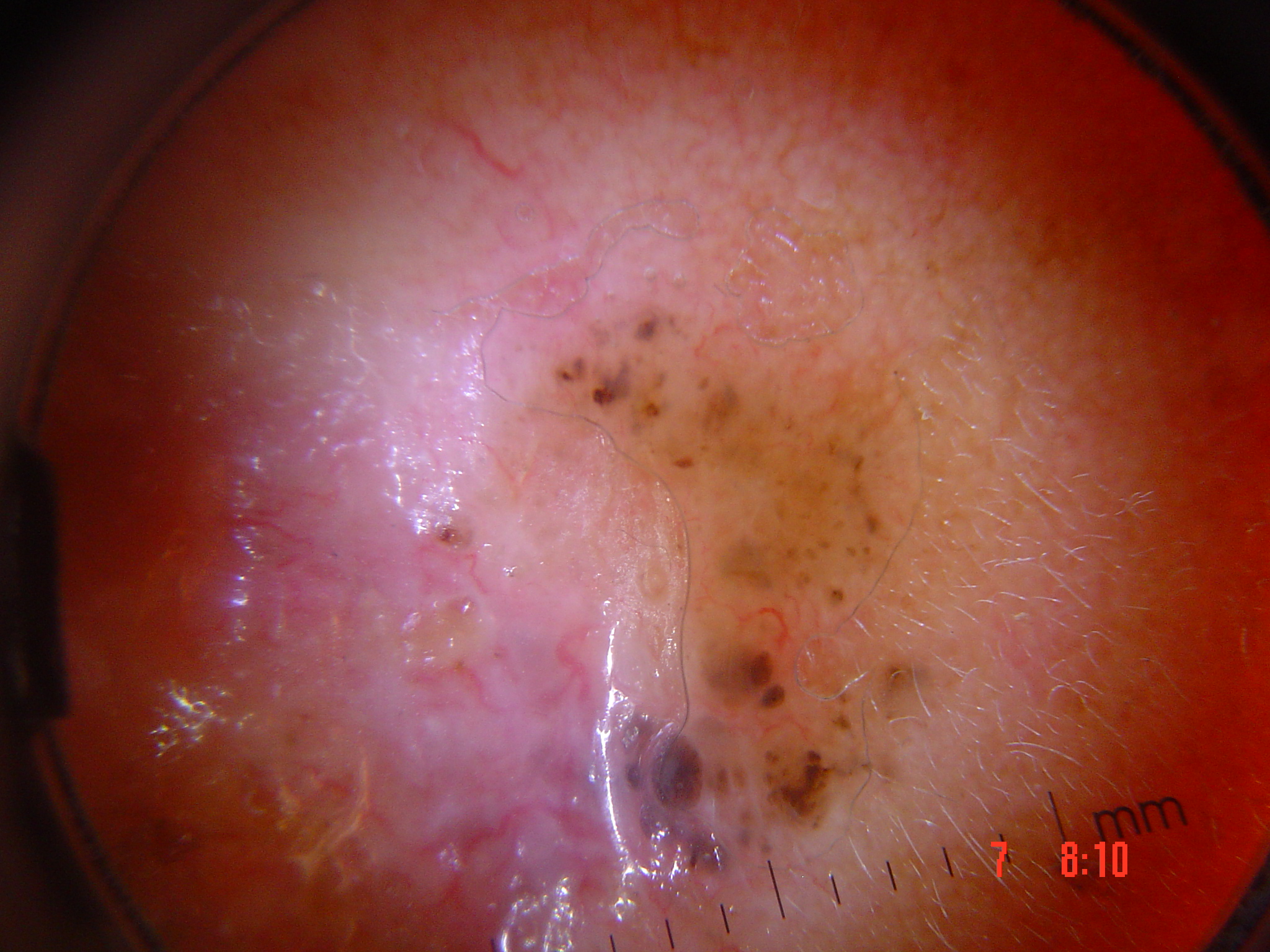Summary:
A dermoscopy image of a single skin lesion. The architecture is that of a keratinocytic lesion.
Conclusion:
Biopsy-confirmed as a basal cell carcinoma.